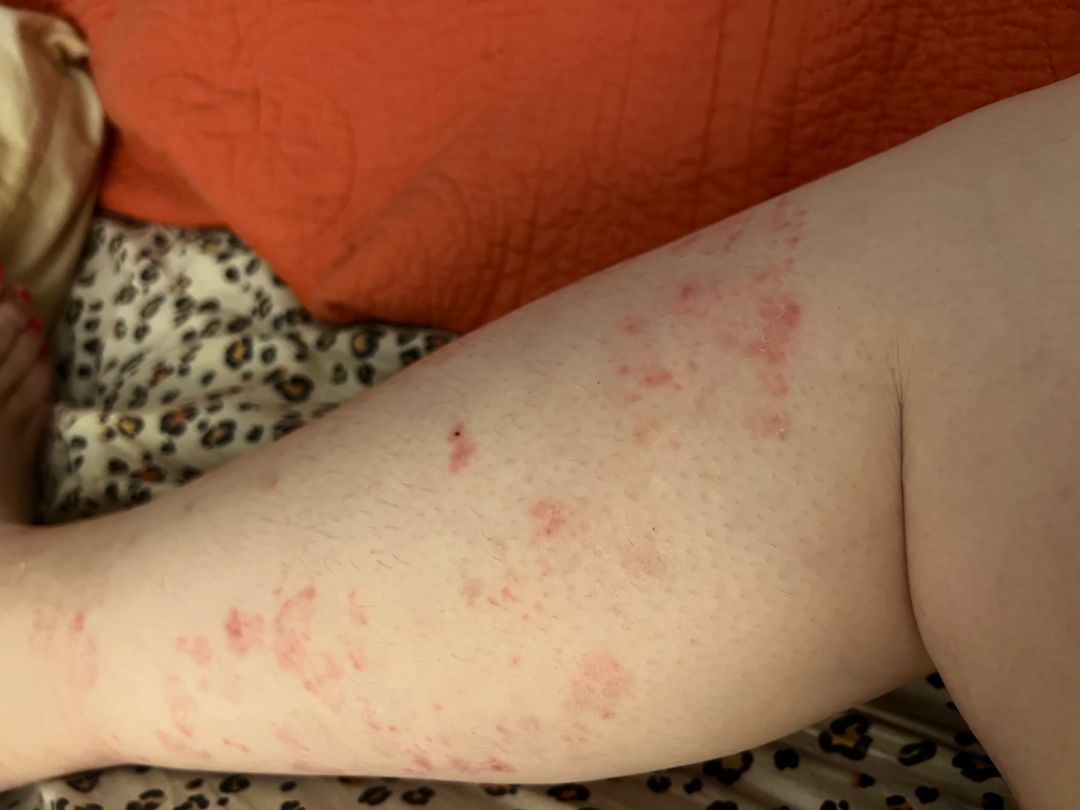texture: rough or flaky, raised or bumpy and flat
anatomic site: leg
onset: more than one year
patient: female, age 30–39
image framing: at an angle
self-categorized as: a rash
diagnostic considerations: Tinea (weight 0.67); Eczema (weight 0.33)